The lesion involves the top or side of the foot · the patient considered this a rash · the photograph was taken at a distance · the patient is 40–49, female — 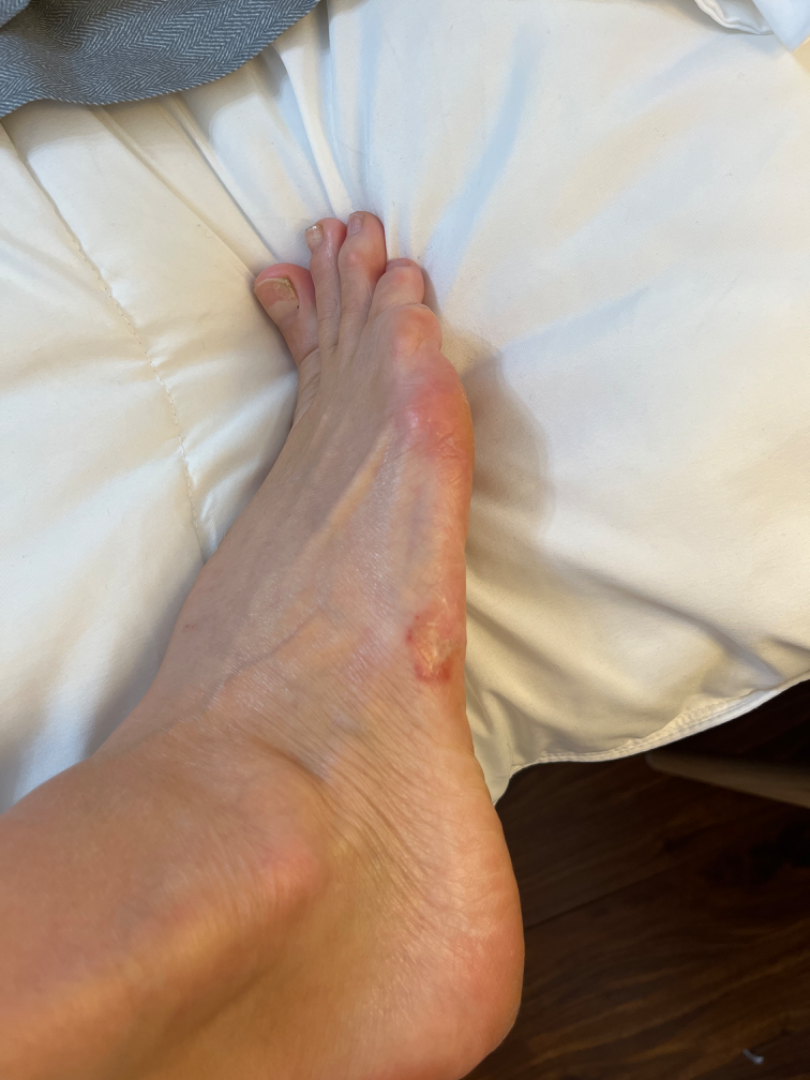Q: What was the assessment?
A: could not be assessed